Collected as part of a research study, without a referral diagnosis; a female subject 81 years of age; the patient says their skin reddens painfully with sun exposure; a dermatoscopic image of a skin lesion; a moderate number of moles by the patient's own estimate; the patient reports no prior organ transplant.
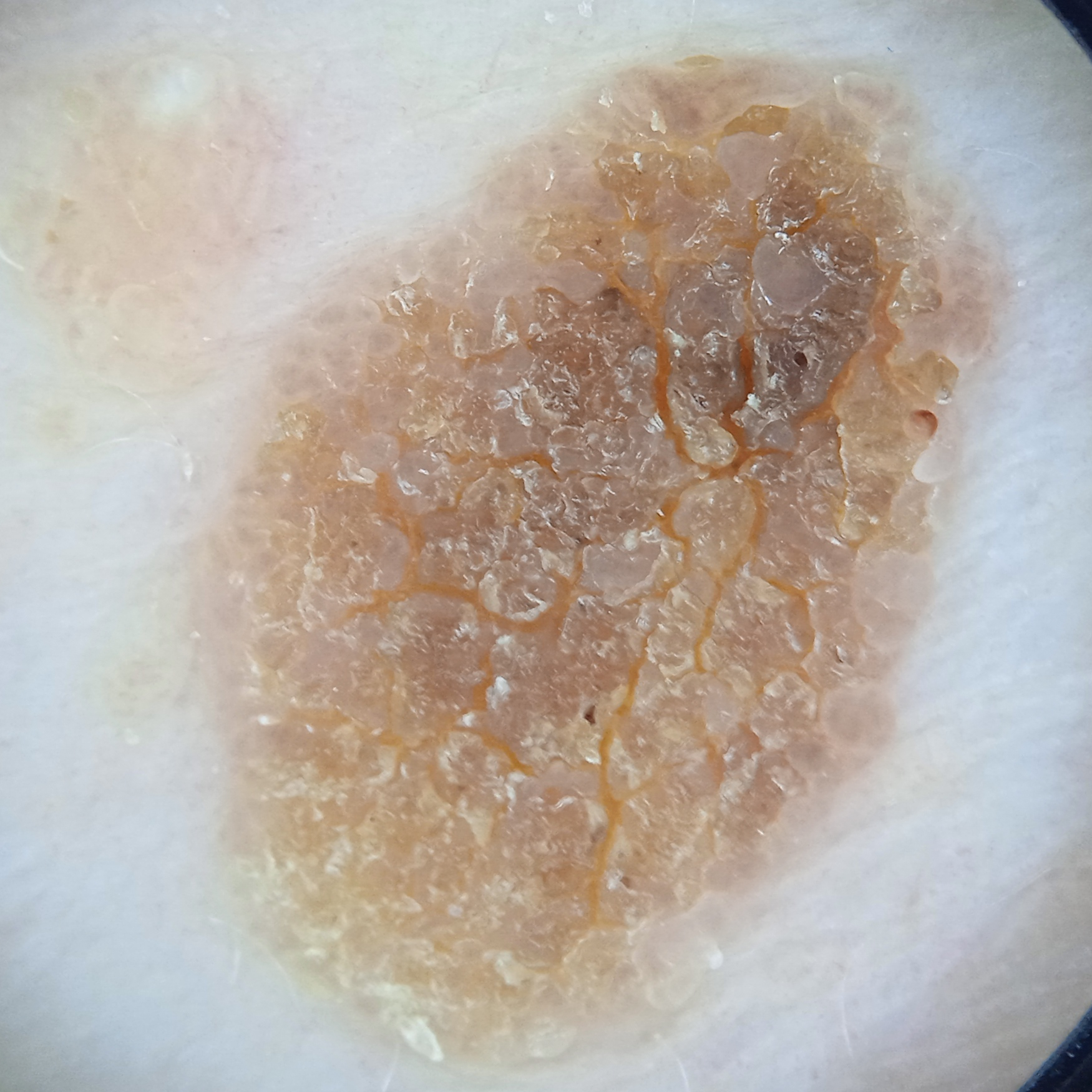Clinical context: Located on the torso. Measuring roughly 12.2 mm. Assessment: Dermatologist review favored a seborrheic keratosis.